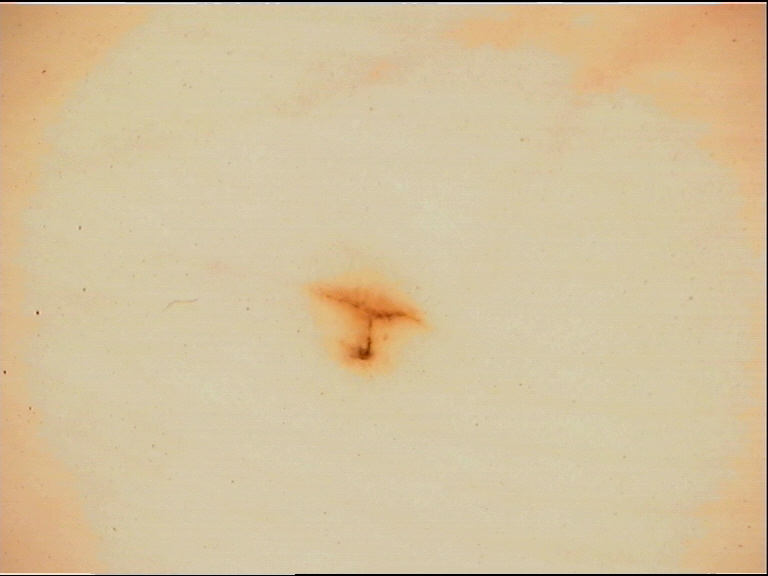The diagnostic label was an acral junctional nevus.